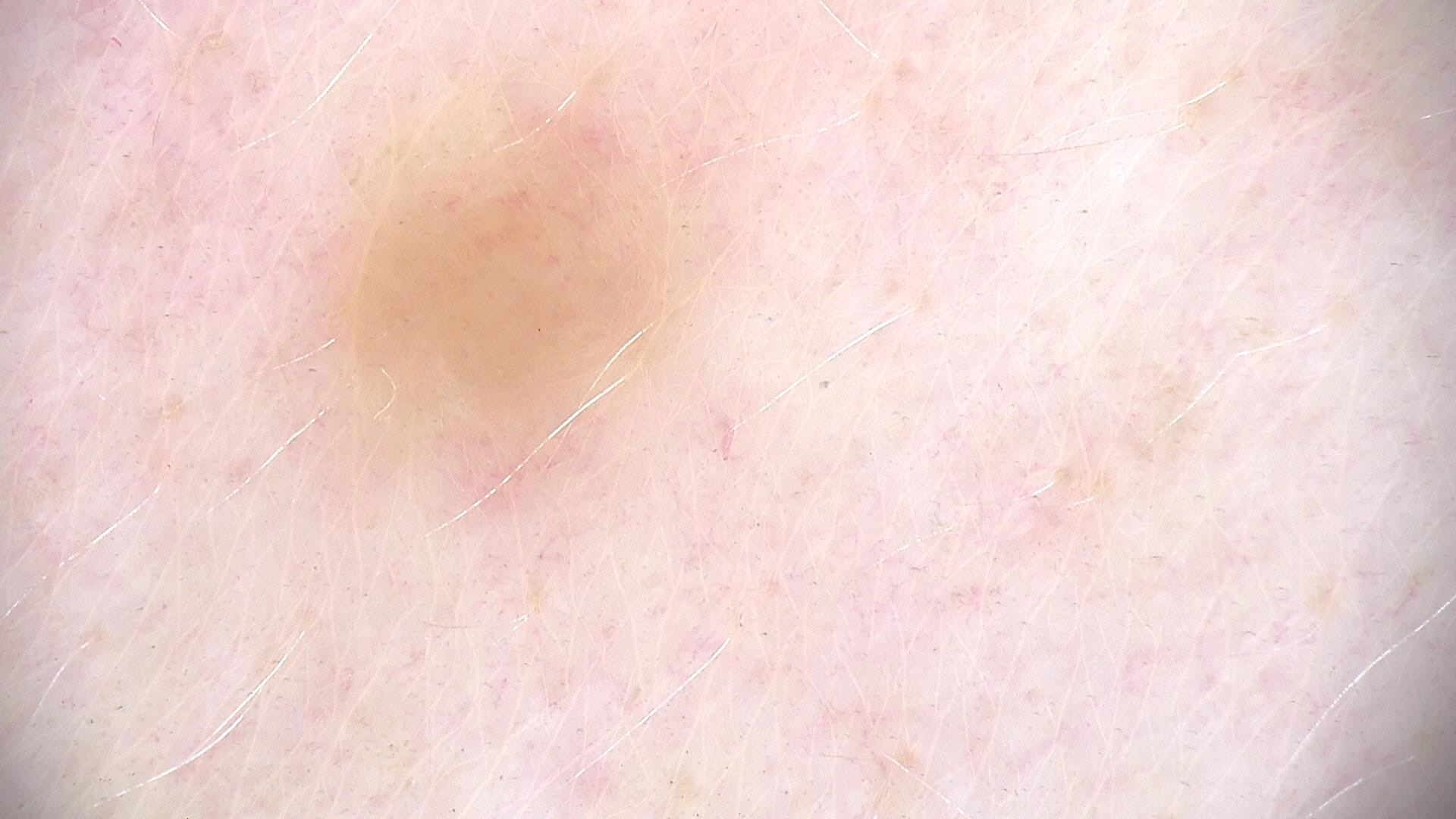Findings: A dermoscopic photograph of a skin lesion. The architecture is that of a banal lesion. Impression: Diagnosed as a dermal nevus.